A clinical close-up photograph of a skin lesion · a patient 72 years old.
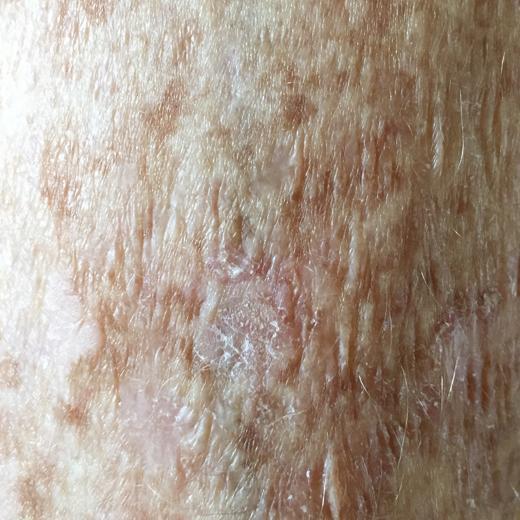The lesion is on a forearm. The patient describes that the lesion itches. The clinical impression was an actinic keratosis.